A dermoscopy image of a single skin lesion: 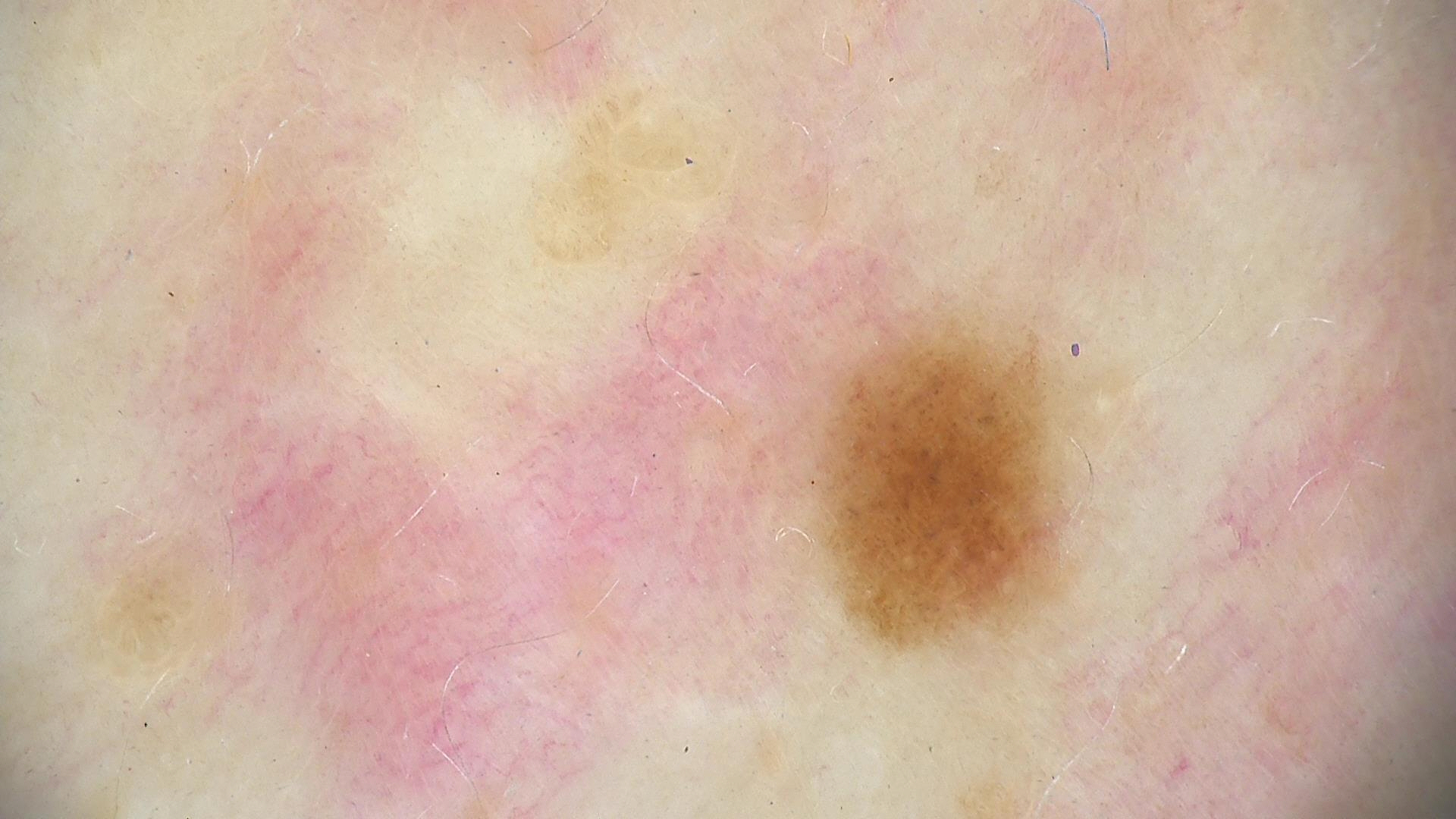The diagnosis was a dysplastic junctional nevus.